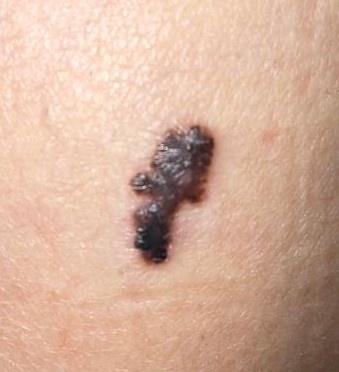Recorded as skin type II. The lesion is on the trunk, specifically the anterior trunk. Histopathology confirmed a basal cell carcinoma.